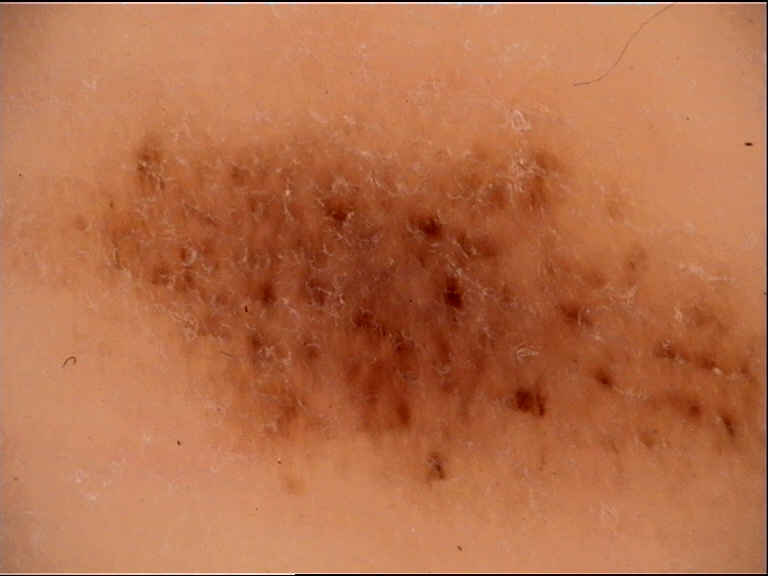Case:
• diagnostic label — acral dysplastic junctional nevus (expert consensus)